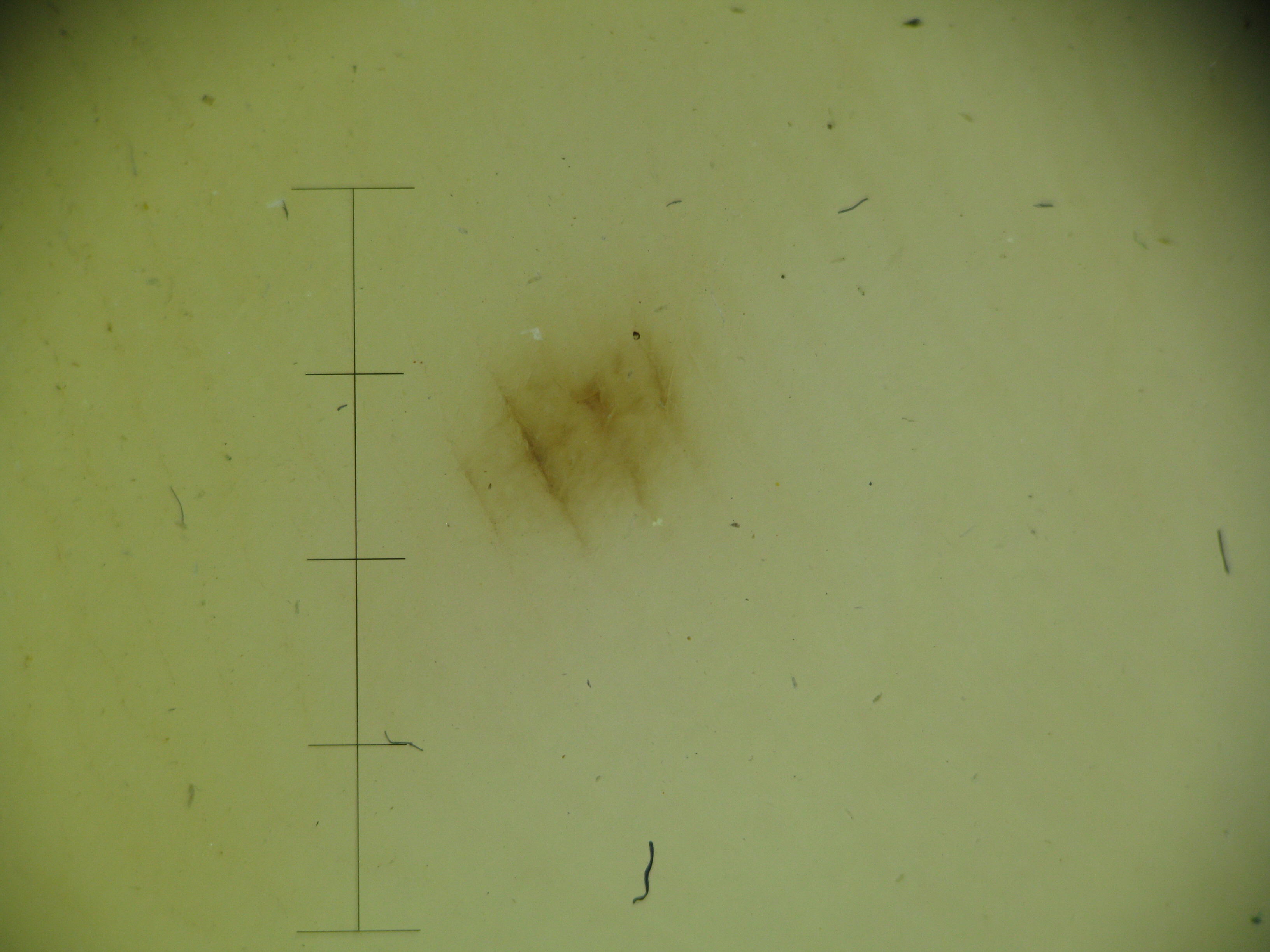A dermoscopic image of a skin lesion. The architecture is that of a banal lesion. Classified as an acral junctional nevus.